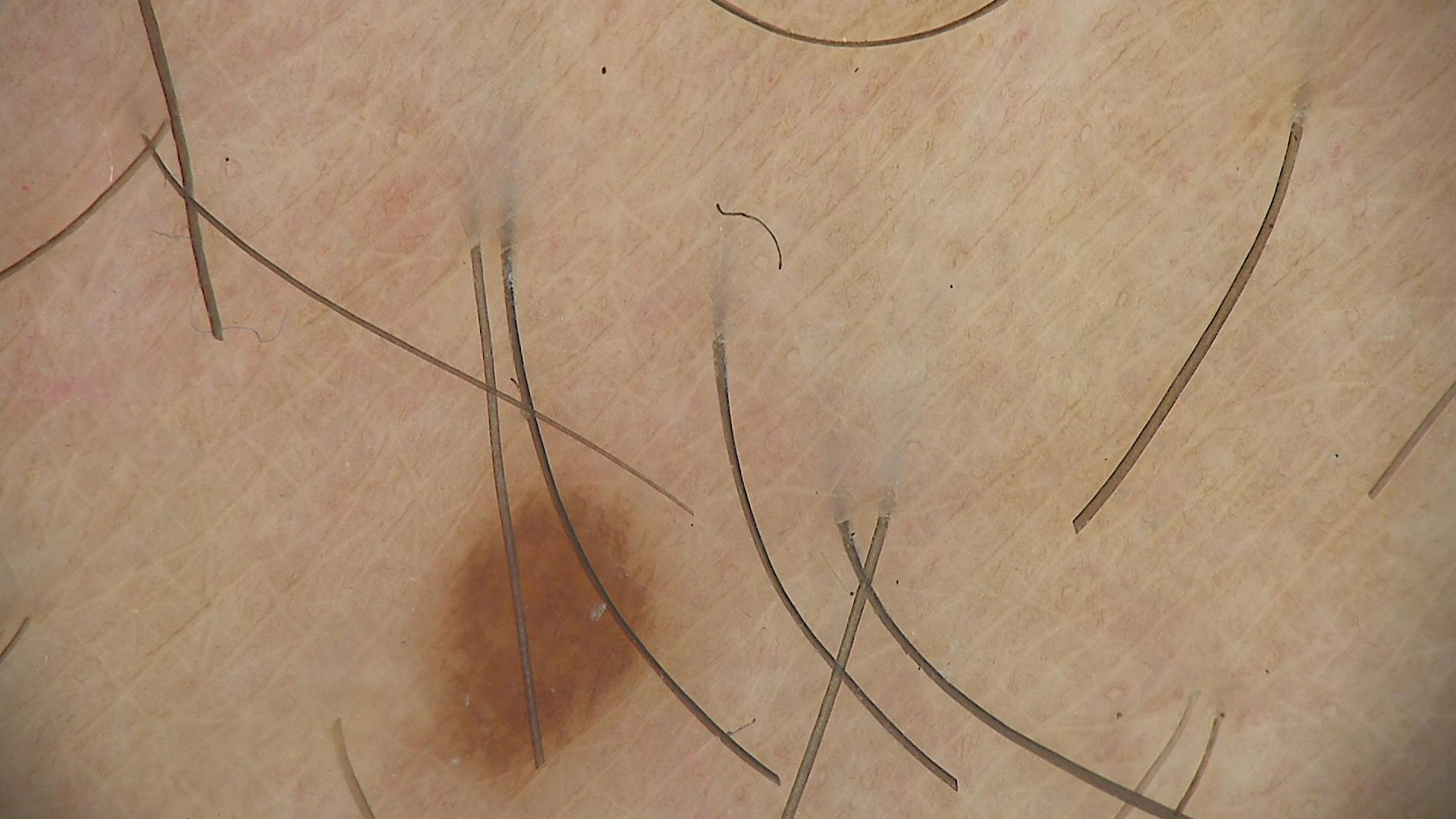A dermoscopic photograph of a skin lesion. Consistent with a banal lesion — a junctional nevus.